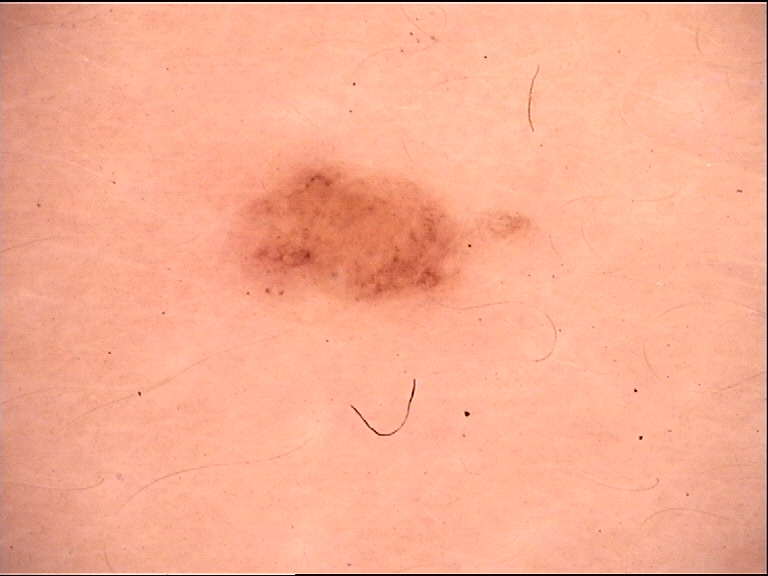Consistent with a dysplastic junctional nevus.